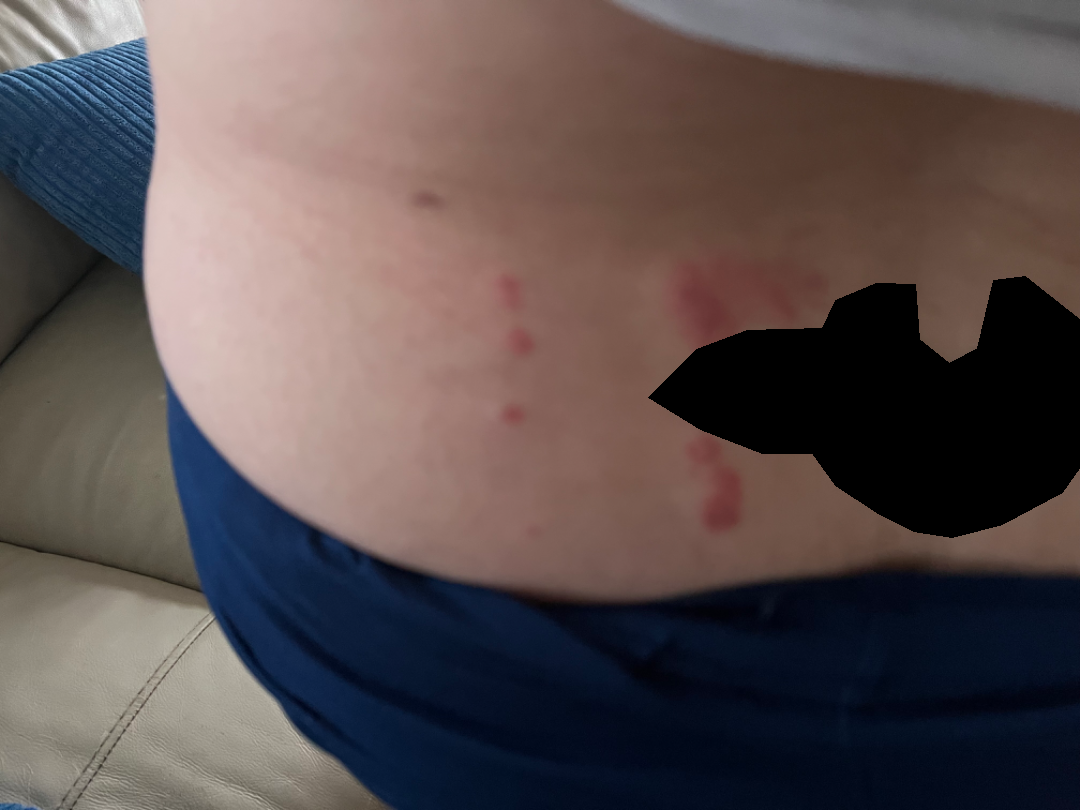Q: Patient's own categorization?
A: a rash
Q: How long has this been present?
A: less than one week
Q: What is the patient's skin tone?
A: Fitzpatrick phototype II; non-clinician graders estimated Monk skin tone scale 2 or 3 (two reviewer pools)
Q: Any systemic symptoms?
A: fatigue and fever
Q: Patient demographics?
A: female, age 50–59
Q: Reported symptoms?
A: burning and itching
Q: What is the affected area?
A: back of the torso
Q: What is the framing?
A: close-up
Q: What is the differential diagnosis?
A: most likely Allergic Contact Dermatitis; possibly Herpes Zoster